Dermoscopy of a skin lesion — 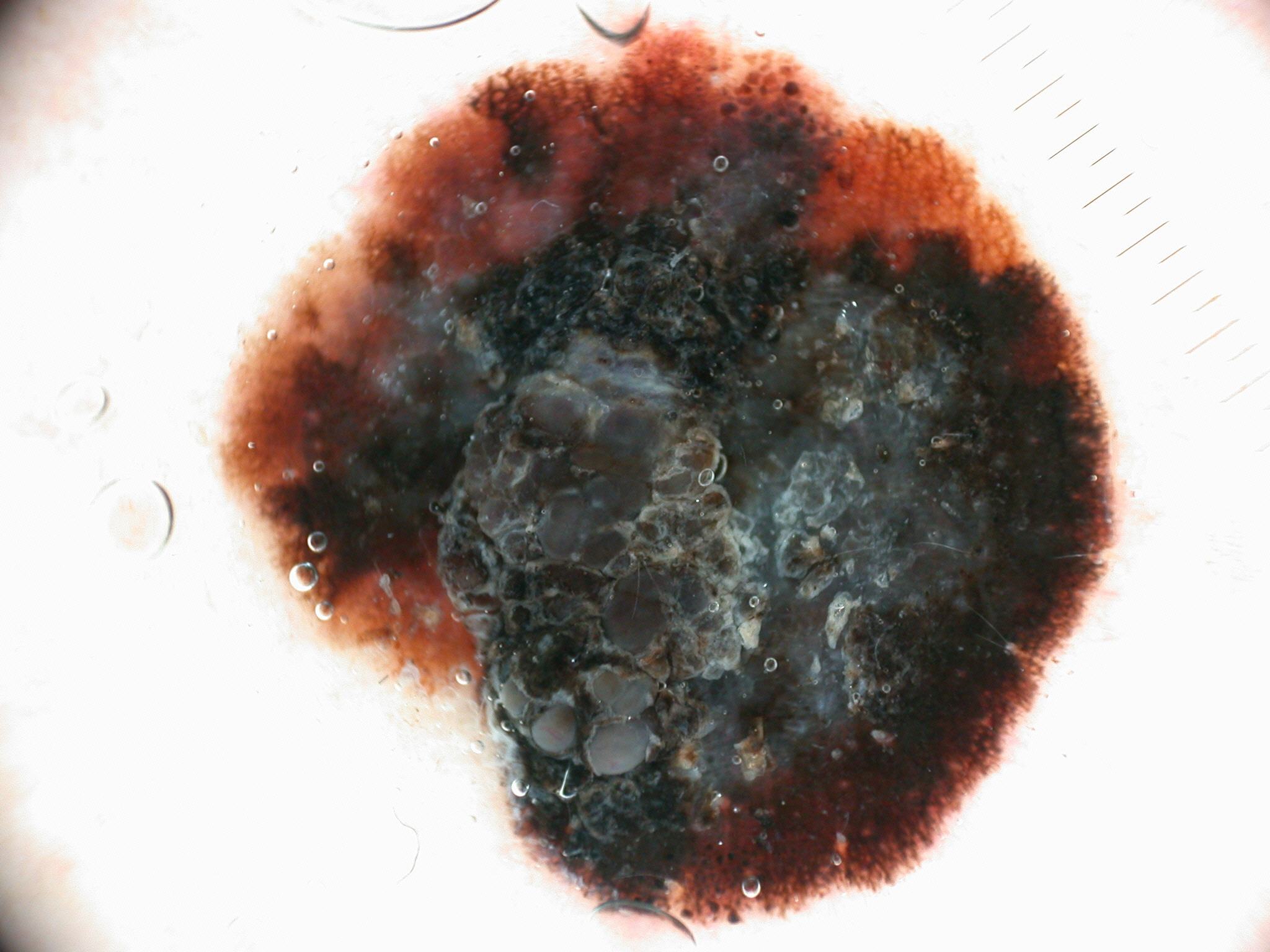Dermoscopic assessment notes globules, streaks, and pigment network; no negative network or milia-like cysts. The lesion occupies the region x1=212, y1=25, x2=1124, y2=932. Histopathologically confirmed as a melanoma.